A dermoscopic image of a skin lesion.
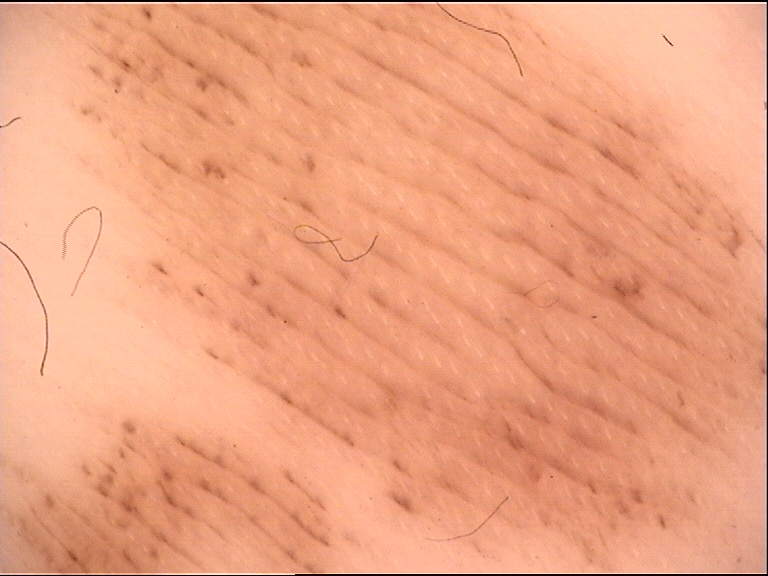Conclusion: Labeled as a banal lesion — an acral junctional nevus.